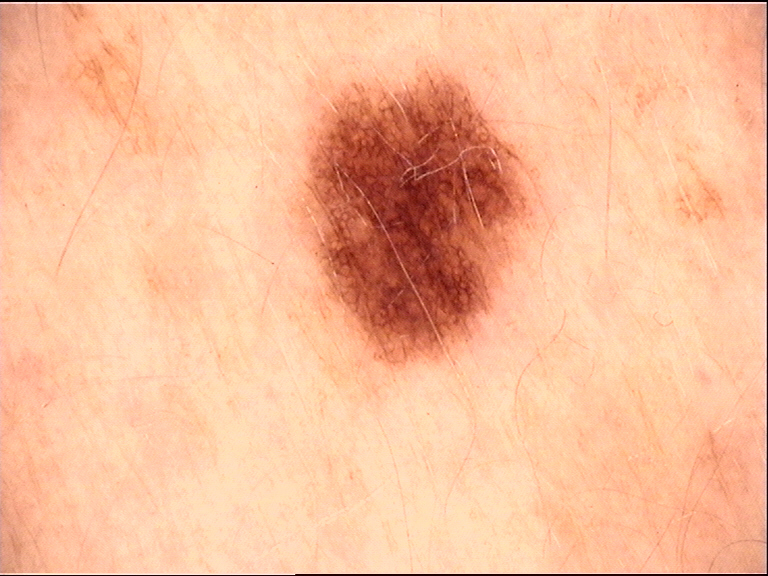Q: What is the diagnosis?
A: dysplastic junctional nevus (expert consensus)